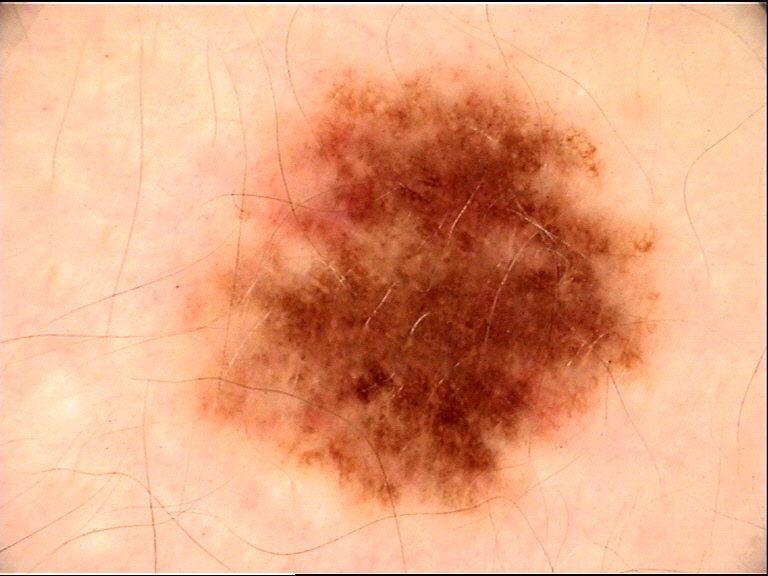• diagnosis · dysplastic junctional nevus (expert consensus)